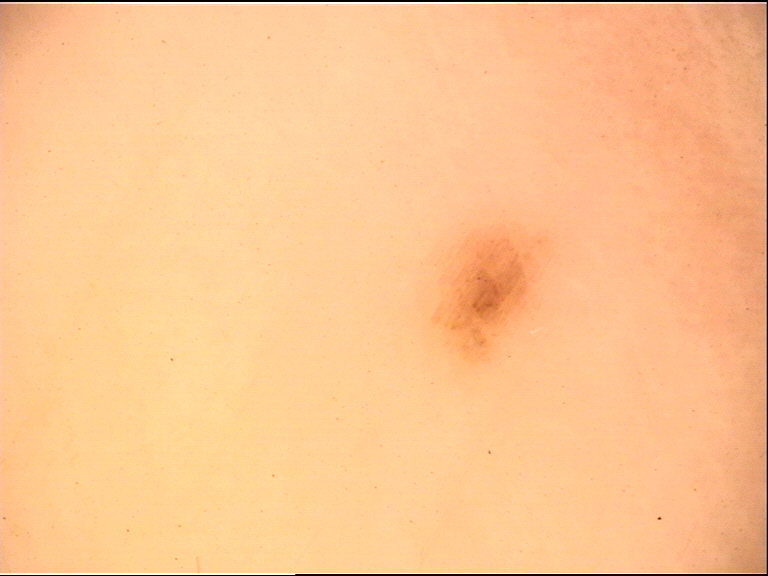Dermoscopy of a skin lesion. The morphology is that of a banal lesion. The diagnosis was an acral junctional nevus.